Female subject, age 18–29 · the head or neck is involved · the photograph was taken at a distance — 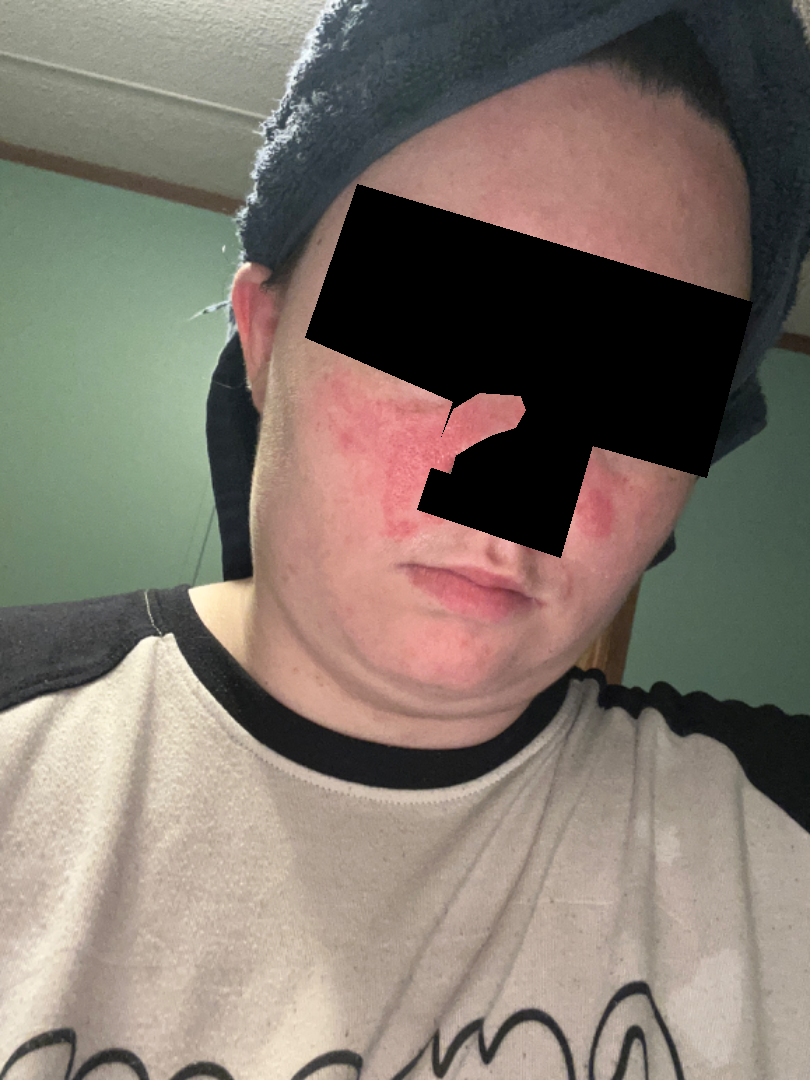Background:
Present for one to three months. Texture is reported as rough or flaky. No associated systemic symptoms reported. The patient considered this a rash.
Findings:
On teledermatology review: Rosacea (leading); Cutaneous lupus (possible); Seborrheic Dermatitis (lower probability); Erysipelas (lower probability).